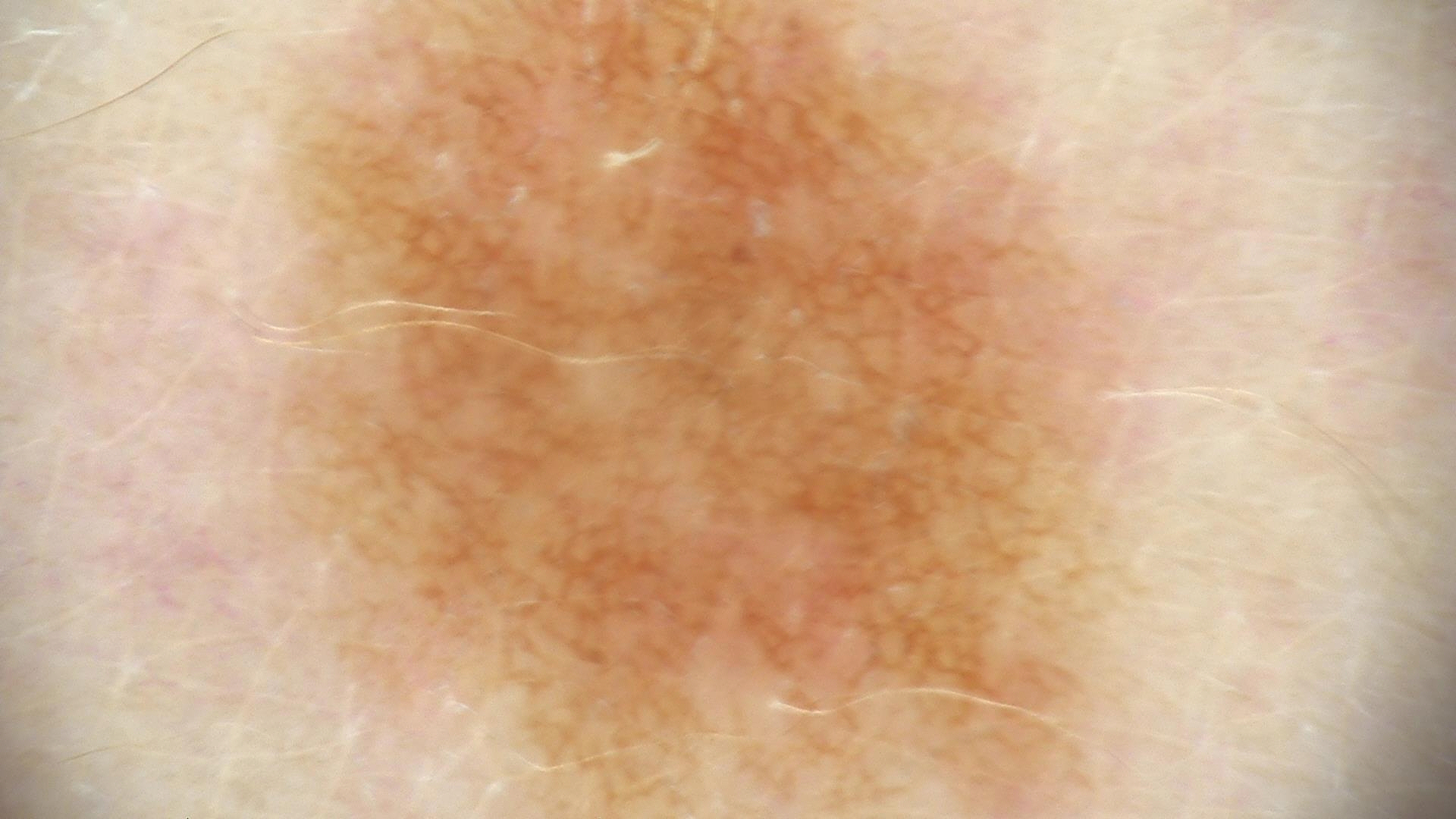  image: dermoscopy
  diagnosis:
    name: junctional nevus
    code: jb
    malignancy: benign
    super_class: melanocytic
    confirmation: expert consensus